A dermoscopy image of a single skin lesion.
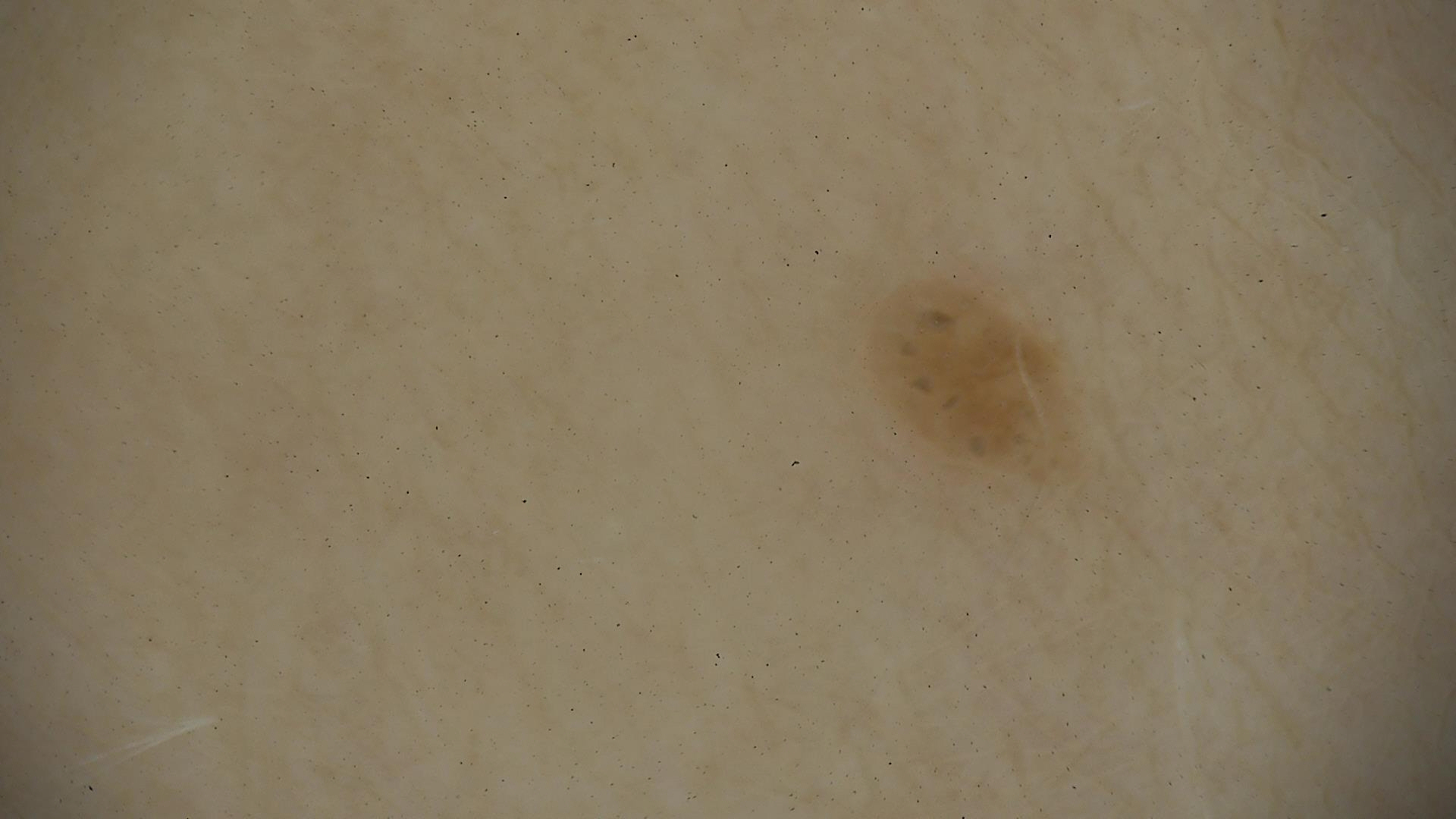Conclusion:
Diagnosed as a keratinocytic, benign lesion — a seborrheic keratosis.